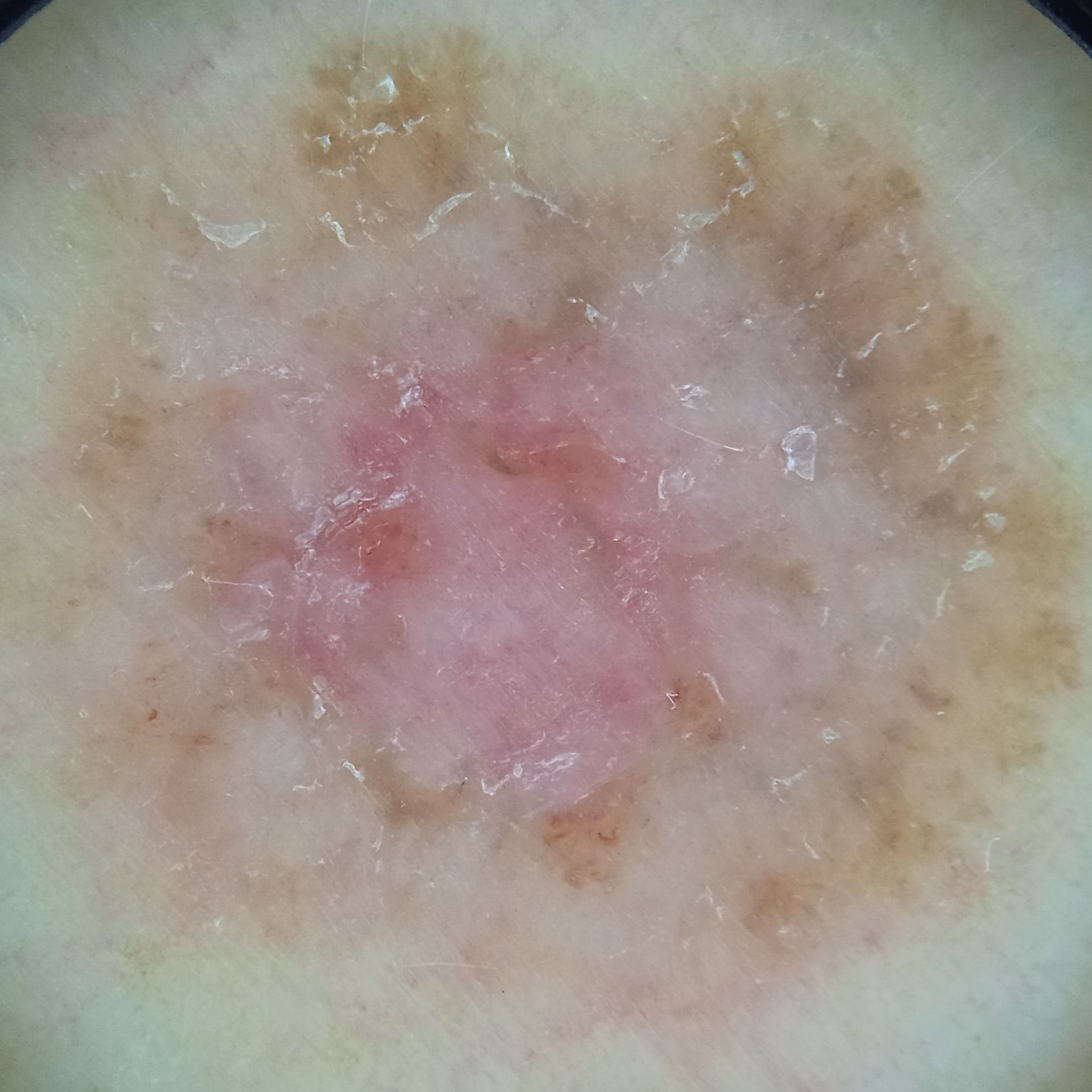Q: Tell me about the patient.
A: female, 60 years of age
Q: What is the patient's nevus burden?
A: few melanocytic nevi overall
Q: How does the patient's skin react to sun?
A: skin tans without first burning
Q: What kind of image is this?
A: dermoscopy
Q: Why was this imaged?
A: clinical suspicion of basal cell carcinoma
Q: Where is the lesion?
A: the torso
Q: What was the diagnosis?
A: basal cell carcinoma (dermatologist consensus)